Located on the back of the torso; the photograph was taken at a distance:
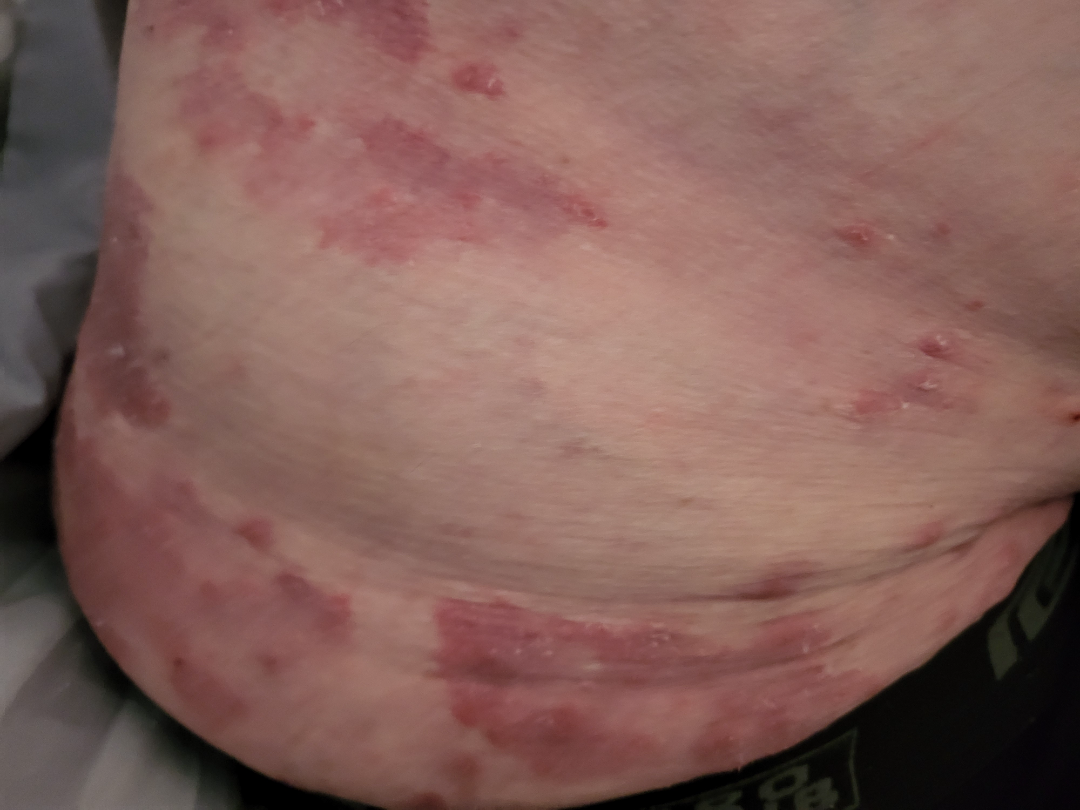Findings:
* present for: about one day
* dermatologist impression: Tinea (weight 0.54); Impetigo (weight 0.23); Folliculitis (weight 0.23)